The leg is involved, the patient is a male aged 60–69, the photo was captured at an angle — 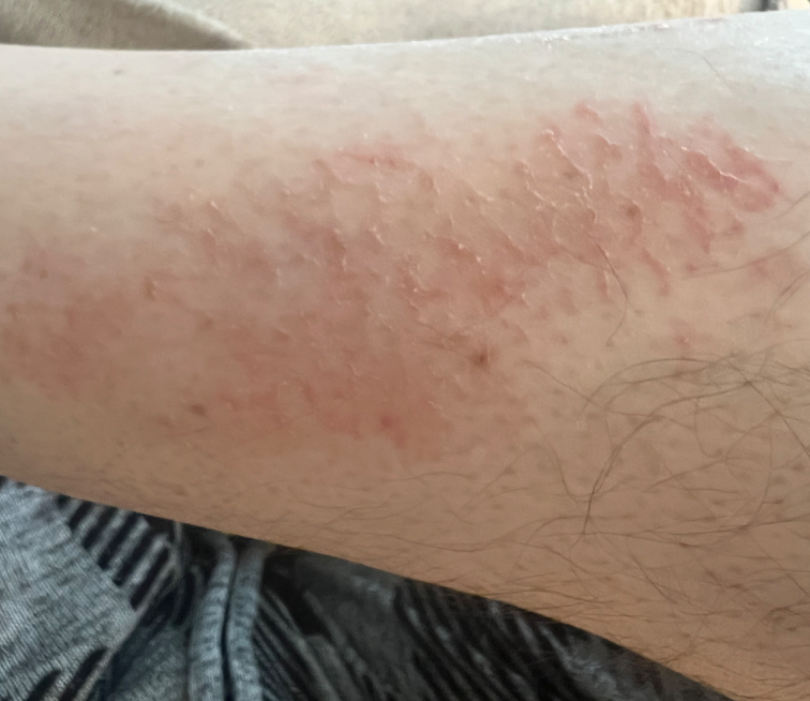Background:
Self-categorized by the patient as a rash. The contributor reports the lesion is rough or flaky. Associated systemic symptoms include shortness of breath and fatigue. Skin tone: Fitzpatrick phototype III; lay graders estimated MST 2. The contributor reports the condition has been present for more than five years.
Findings:
In keeping with Eczema.